A dermoscopic photograph of a skin lesion:
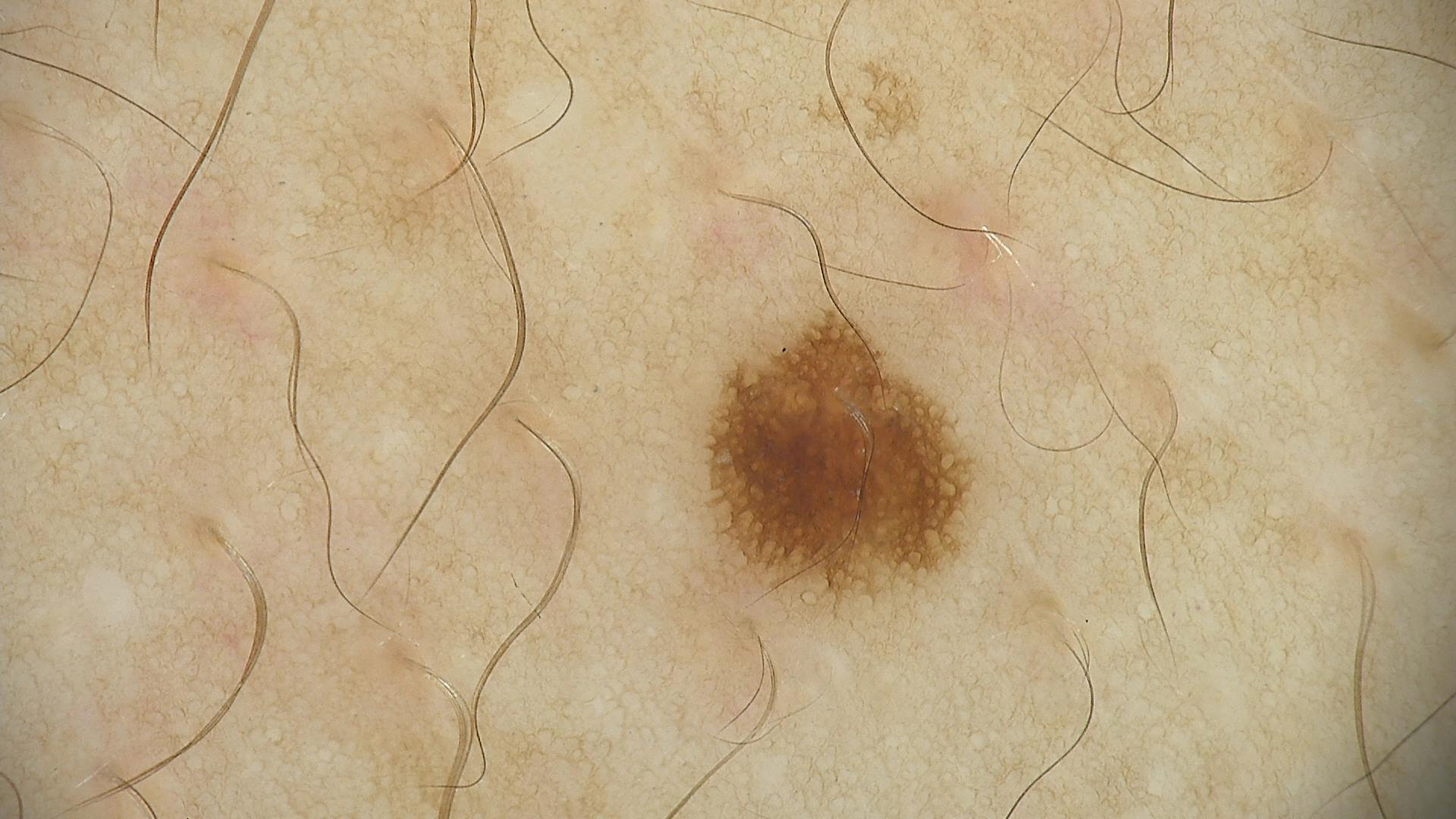label: dysplastic junctional nevus (expert consensus)